A dermoscopy image of a single skin lesion.
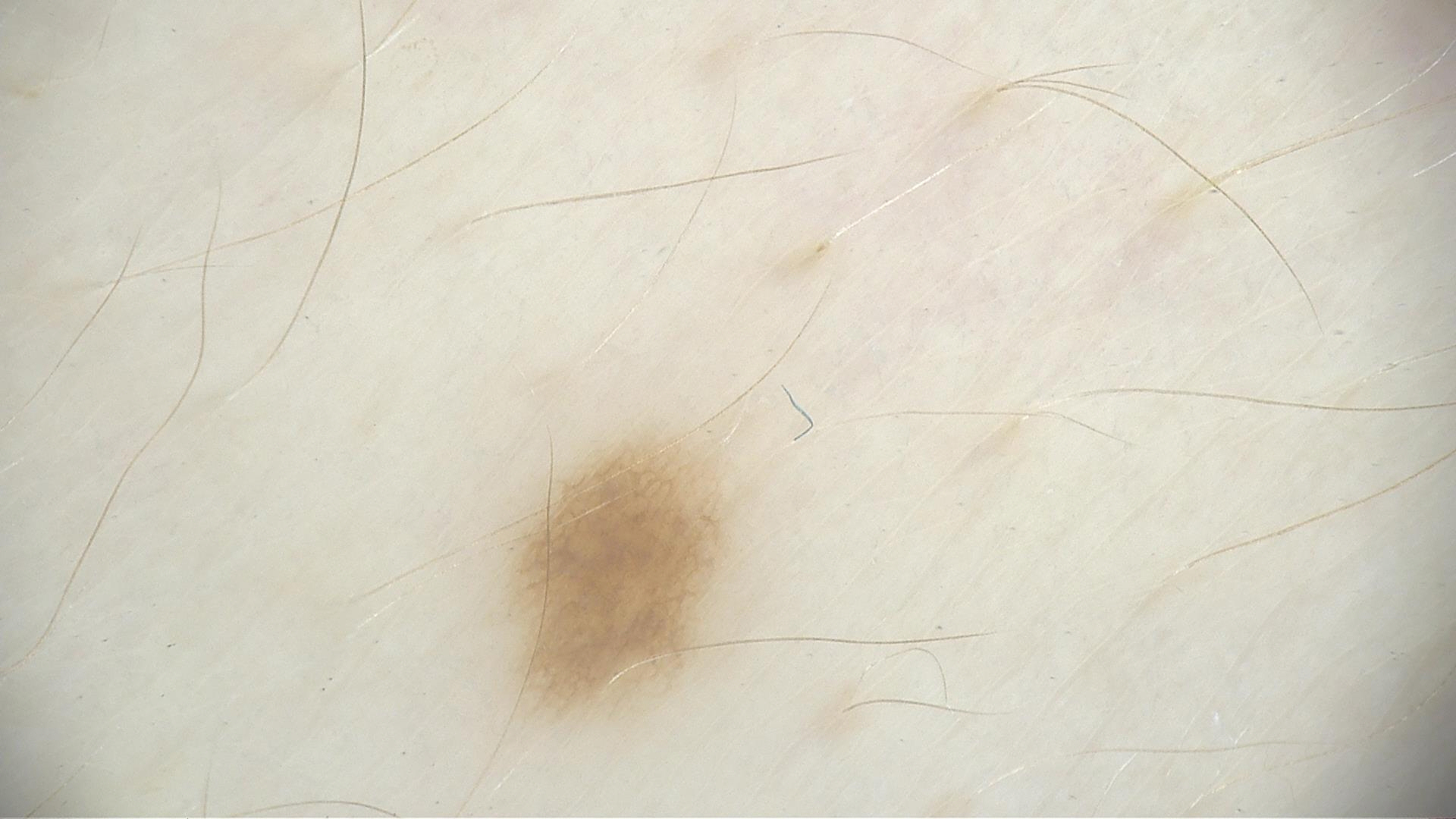Labeled as a junctional nevus.